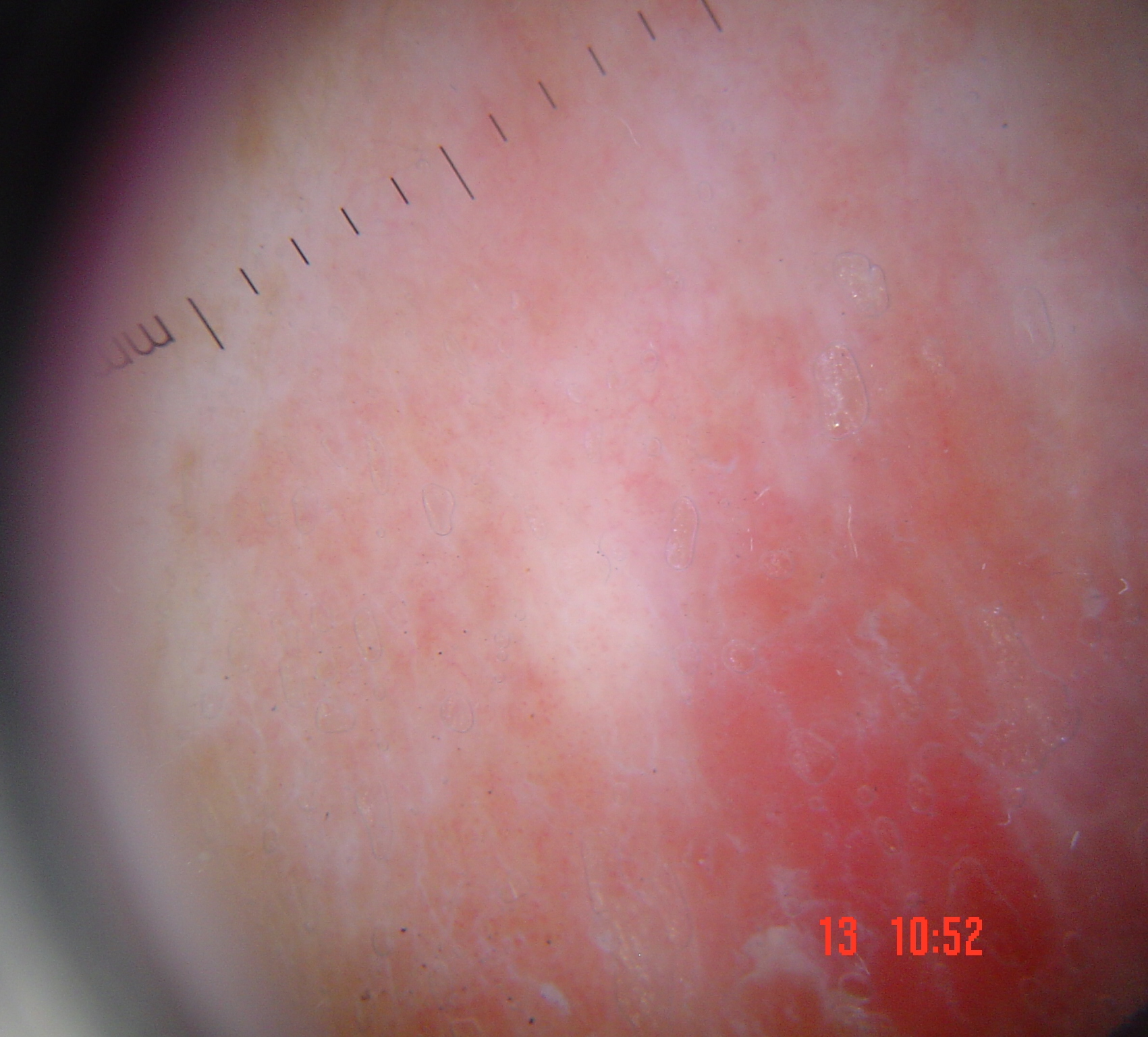image: dermatoscopy
lesion_type:
  main_class: keratinocytic
diagnosis:
  name: Bowen's disease
  code: bd
  malignancy: malignant
  super_class: non-melanocytic
  confirmation: histopathology